This image was taken at a distance · the condition has been present for less than one week · reported lesion symptoms include itching · the back of the hand, arm and leg are involved · texture is reported as fluid-filled and raised or bumpy · the patient described the issue as a rash · skin tone: non-clinician graders estimated Monk skin tone scale 3 or 4 · female contributor, age 40–49: 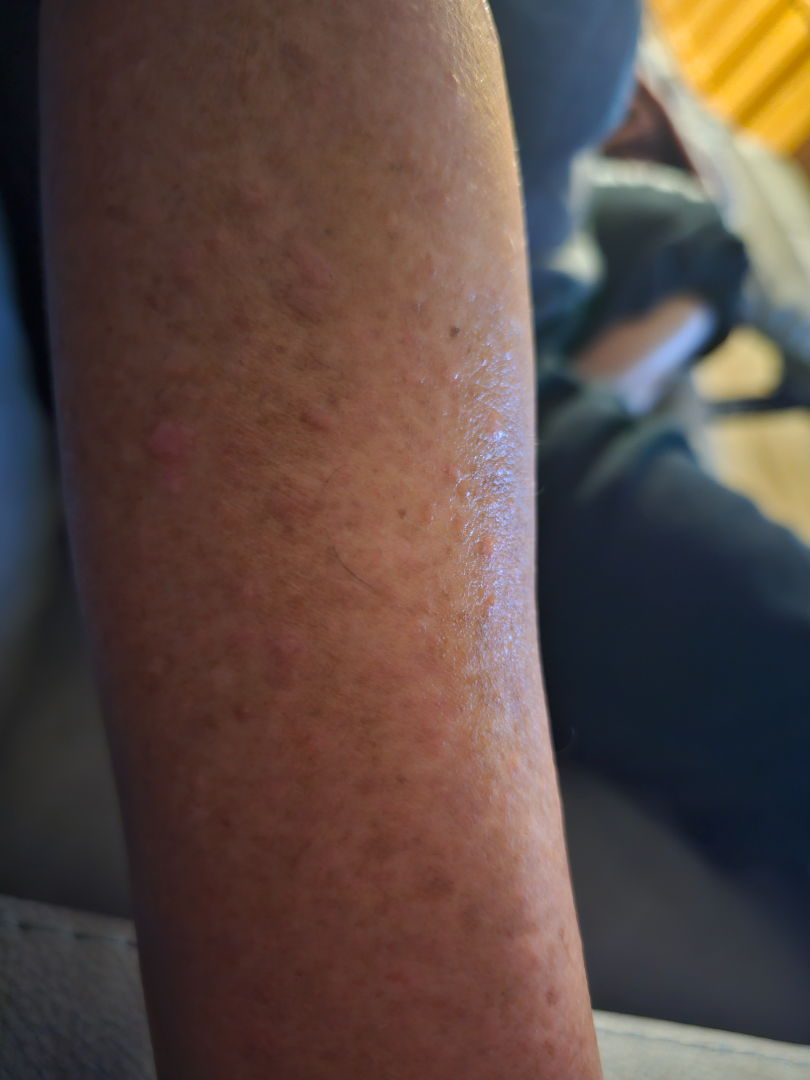dermatologist impression = Stasis Dermatitis (primary)